A dermoscopic image of a skin lesion:
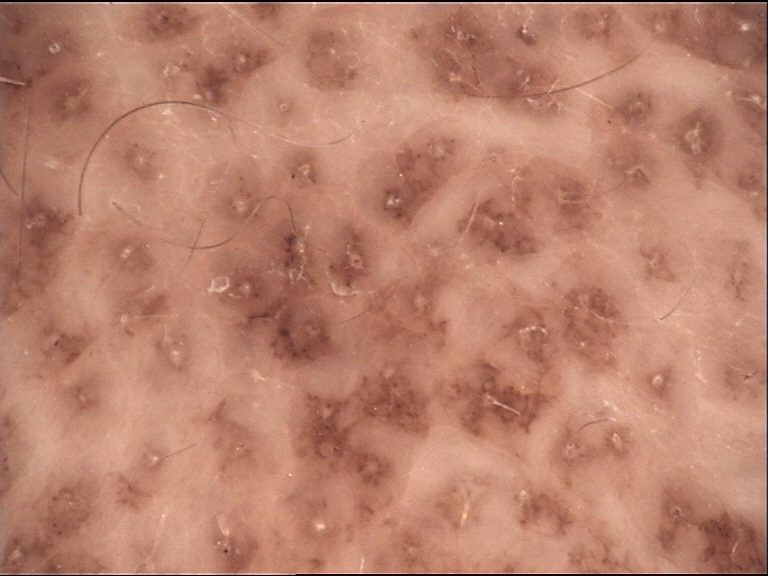Labeled as a banal lesion — a congenital compound nevus.